An image taken at a distance · the lesion involves the back of the torso — 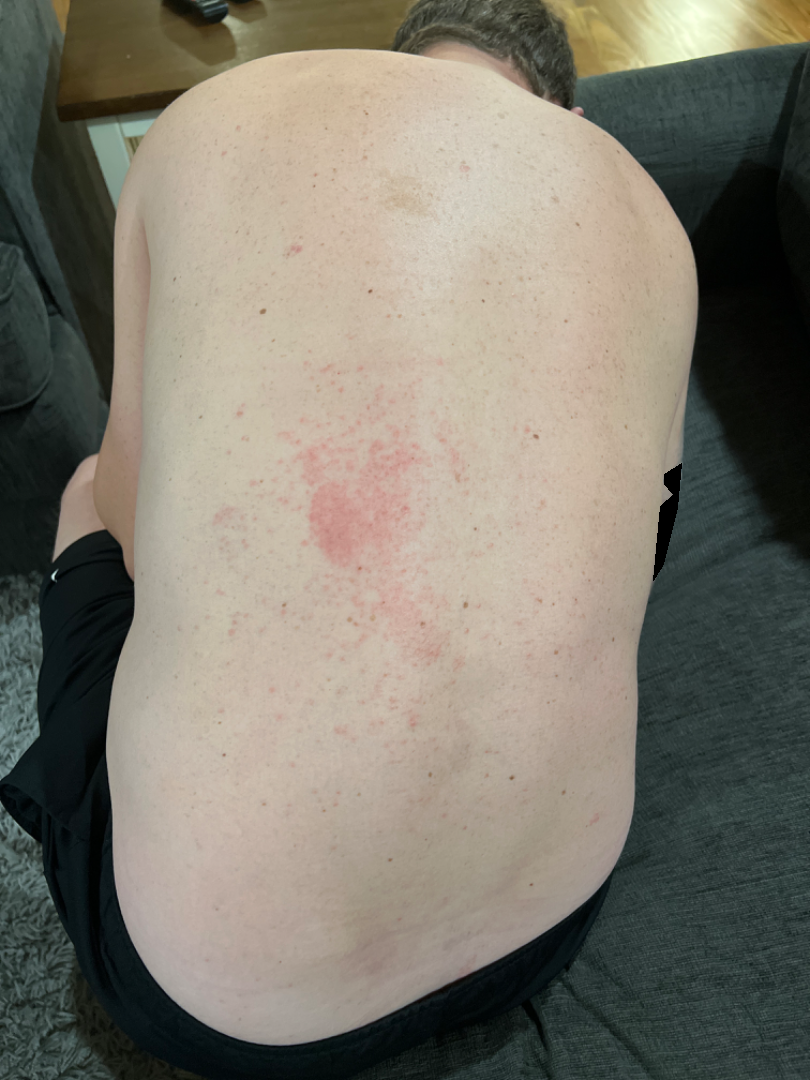Q: What symptoms does the patient report?
A: itching
Q: When did this start?
A: less than one week
Q: Patient's own categorization?
A: a rash
Q: Texture?
A: raised or bumpy and flat
Q: What is the dermatologist's impression?
A: Acute dermatitis, NOS and Allergic Contact Dermatitis were considered with similar weight